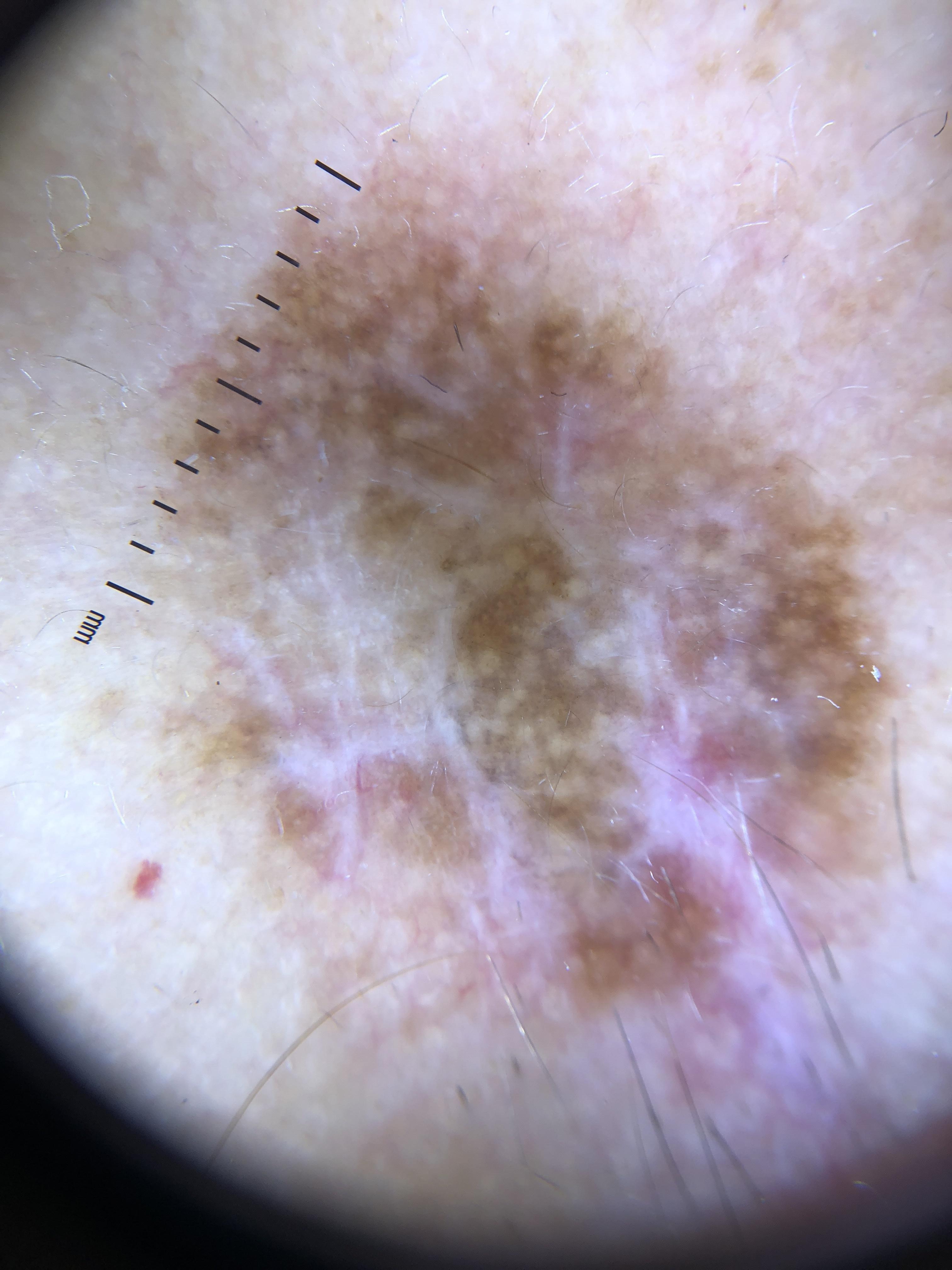Image and clinical context:
The patient is skin type II. The chart notes a prior melanoma. A female patient aged 43 to 47. A dermoscopic close-up of a skin lesion. The lesion is located on the head or neck.
Conclusion:
Biopsy-confirmed as a malignant lesion — a melanoma.